This is a close-up image. No constitutional symptoms were reported. Texture is reported as raised or bumpy. The leg is involved. Reported lesion symptoms include itching — 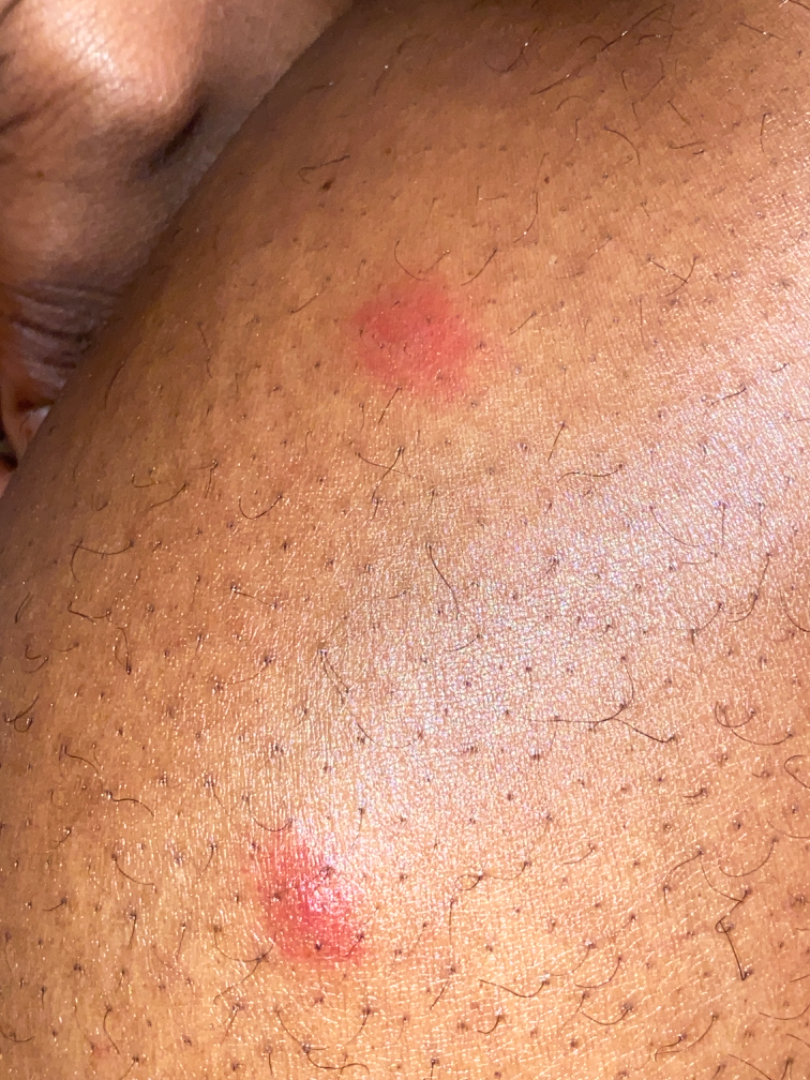assessment — unable to determine.